Dermoscopy of a skin lesion:
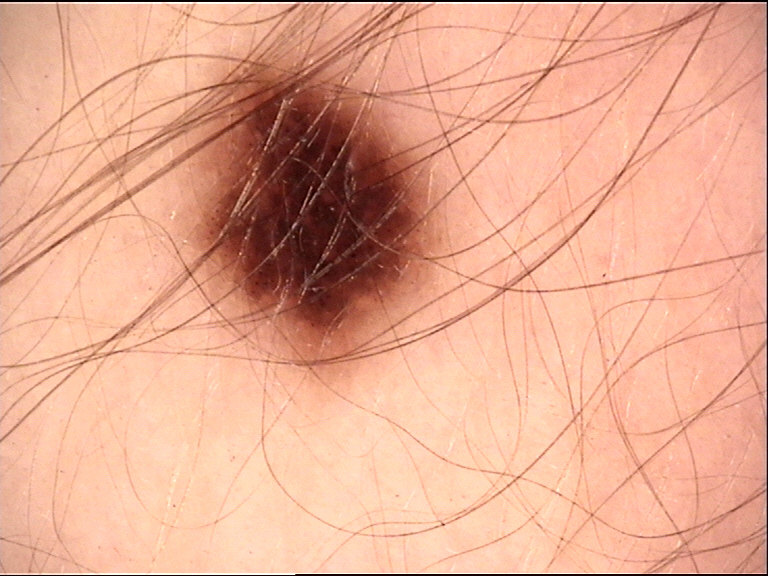{"diagnosis": {"name": "dysplastic junctional nevus", "code": "jd", "malignancy": "benign", "super_class": "melanocytic", "confirmation": "expert consensus"}}